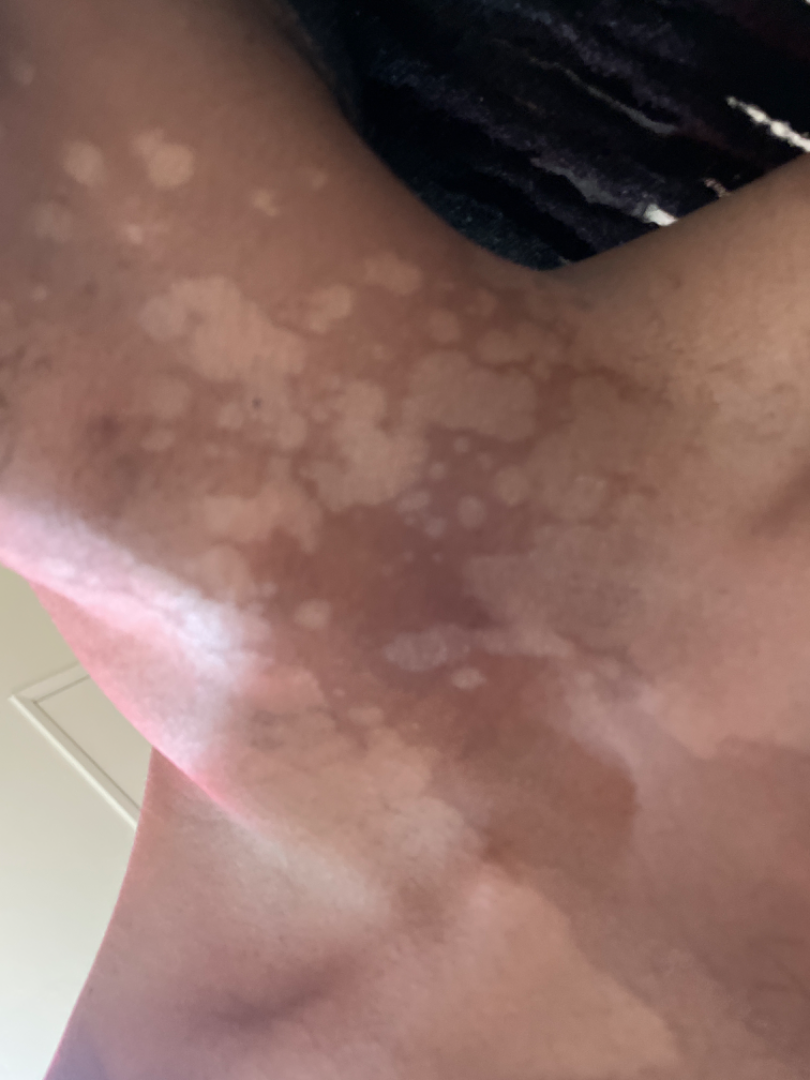The dermatologist could not determine a likely condition from the photograph alone.
Texture is reported as rough or flaky and flat.
This image was taken at an angle.
Self-categorized by the patient as a rash.
Reported lesion symptoms include itching, bothersome appearance and enlargement.
The lesion involves the head or neck.